Dermoscopy of a skin lesion: 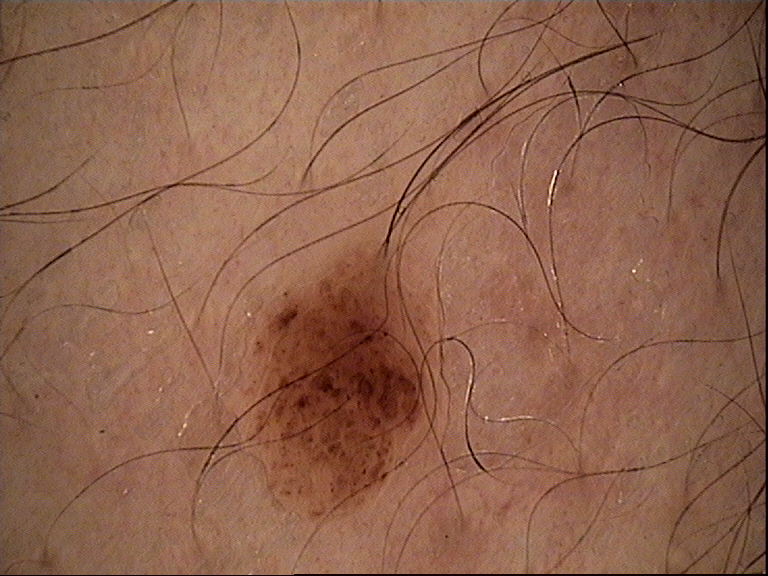The morphology is that of a banal lesion.
Classified as a compound nevus.